The affected area is the leg · an image taken at an angle · the lesion is described as flat and rough or flaky · present for about one day · the subject is a female aged 30–39: 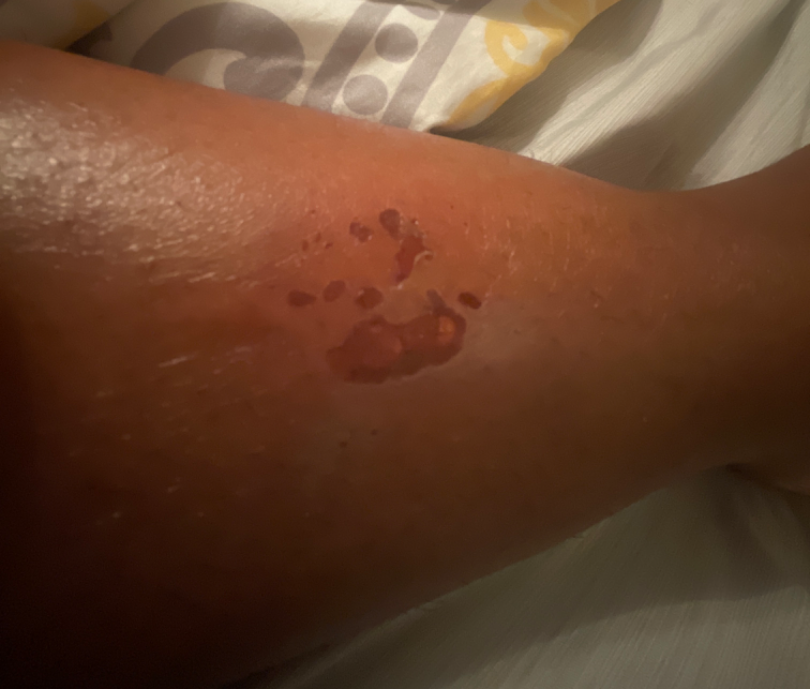On remote review of the image: the differential includes Stasis Dermatitis and Abrasion, scrape, or scab, with no clear leading consideration.